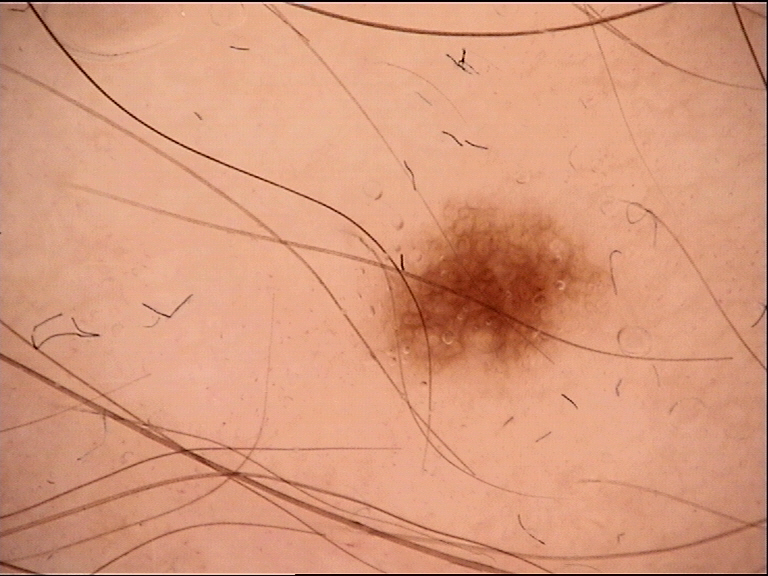Findings:
* modality: dermatoscopy
* lesion type: banal
* diagnostic label: junctional nevus (expert consensus)